A dermatoscopic image of a skin lesion.
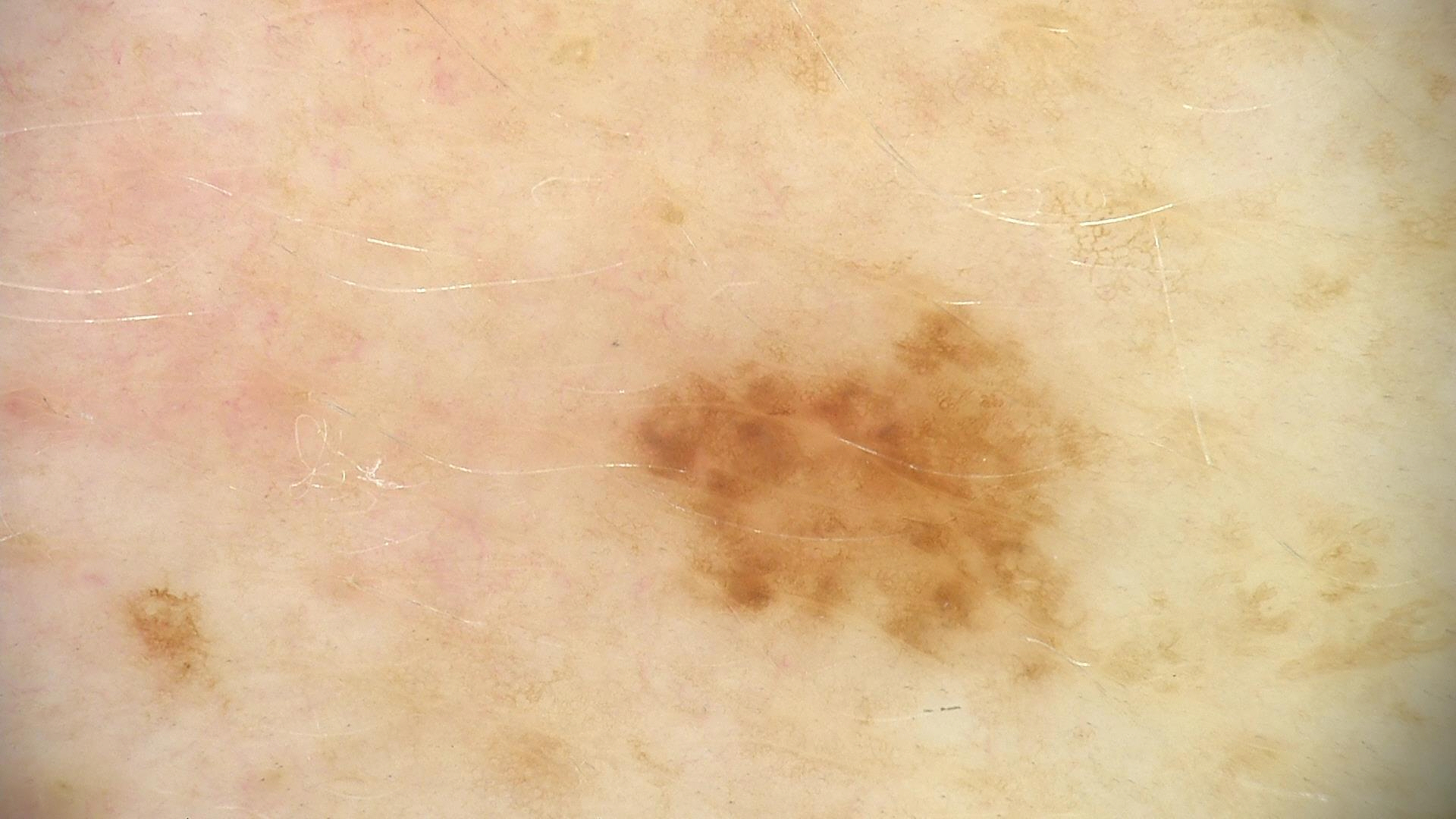  diagnosis:
    name: dysplastic junctional nevus
    code: jd
    malignancy: benign
    super_class: melanocytic
    confirmation: expert consensus